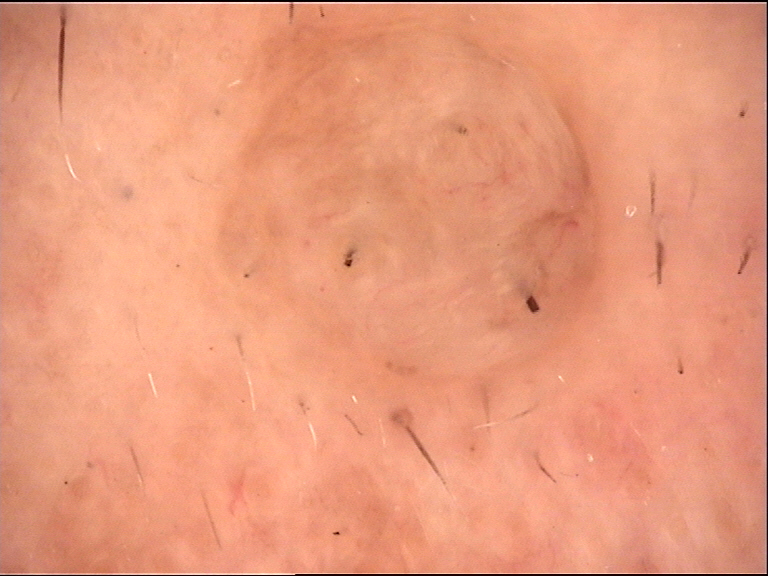{"diagnosis": {"name": "dermal nevus", "code": "db", "malignancy": "benign", "super_class": "melanocytic", "confirmation": "expert consensus"}}